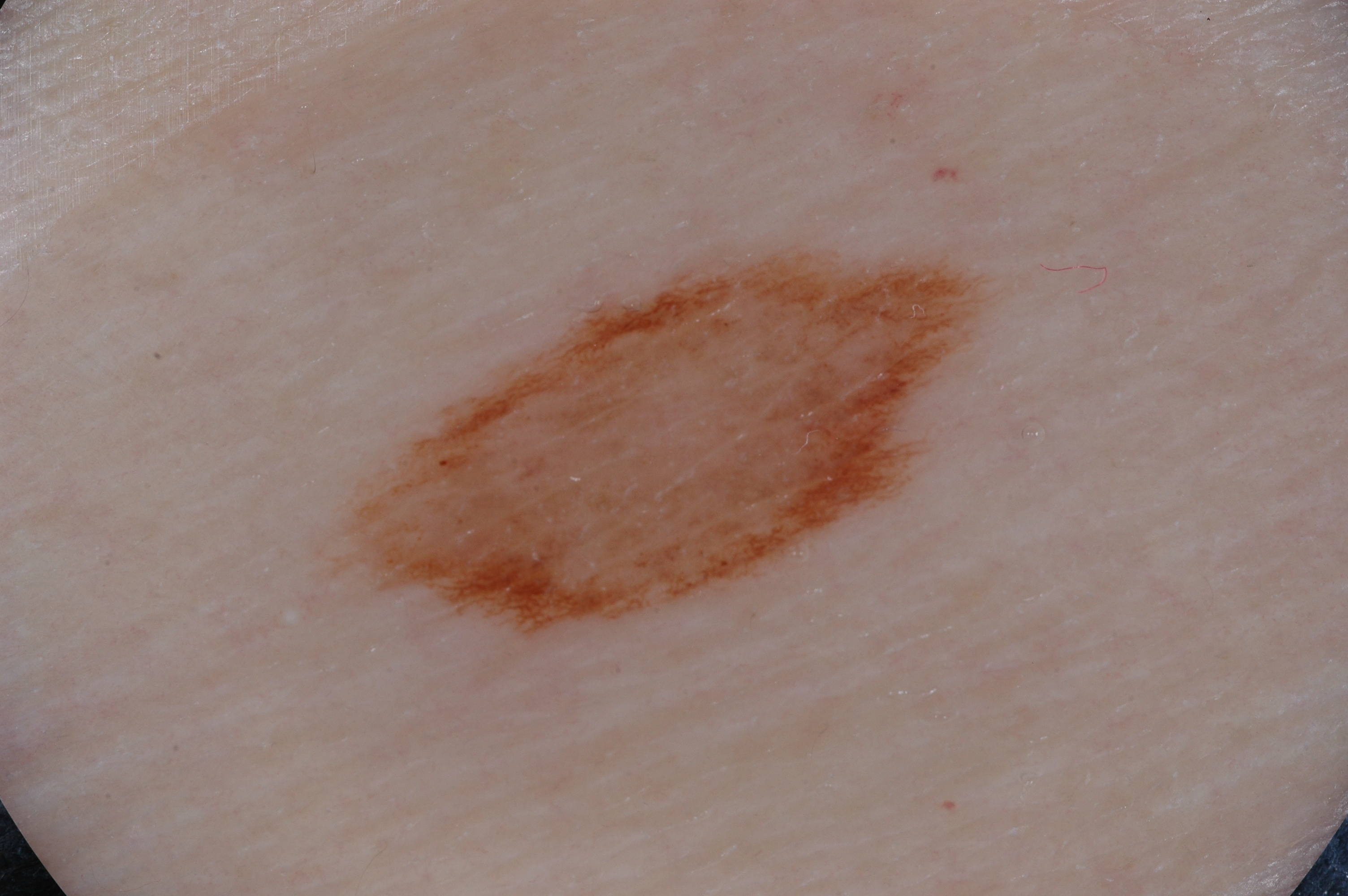A dermoscopic image of a skin lesion. Dermoscopy demonstrates pigment network. The lesion spans x1=312 y1=233 x2=1015 y2=690. The lesion takes up a moderate portion of the field. The lesion was assessed as a melanocytic nevus, a benign skin lesion.